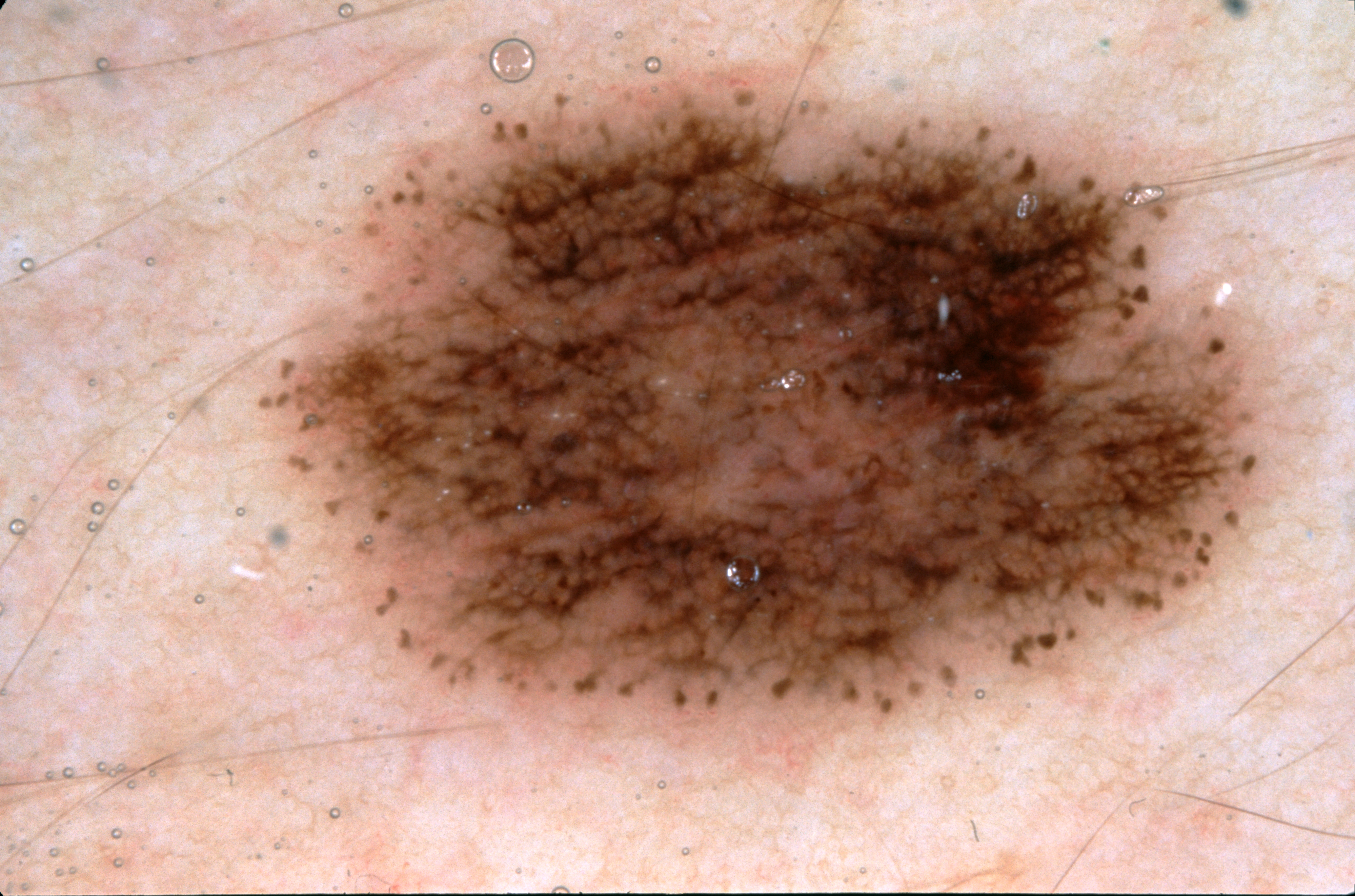Case summary:
– subject — female, aged 28-32
– modality — dermoscopic image
– dermoscopic findings — pigment network; absent: milia-like cysts, negative network, and streaks
– bounding box — 257, 56, 1280, 738
– assessment — a melanocytic nevus, a benign skin lesion